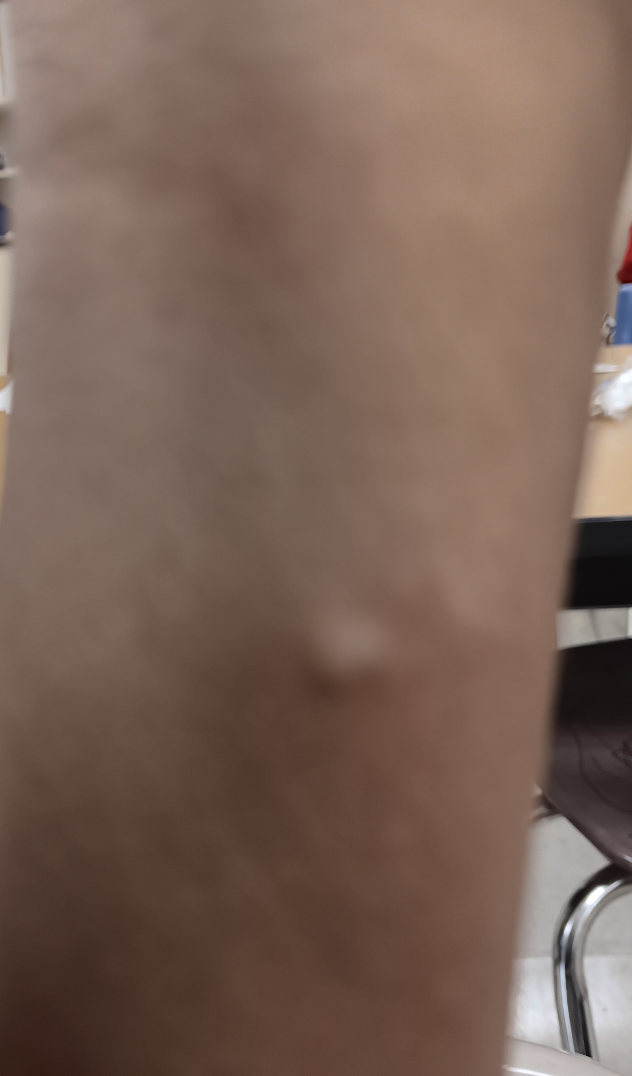{"shot_type": "close-up", "differential": {"leading": ["Cyst"], "considered": ["Calcinosis cutis"]}}